A dermoscopic photograph of a skin lesion: 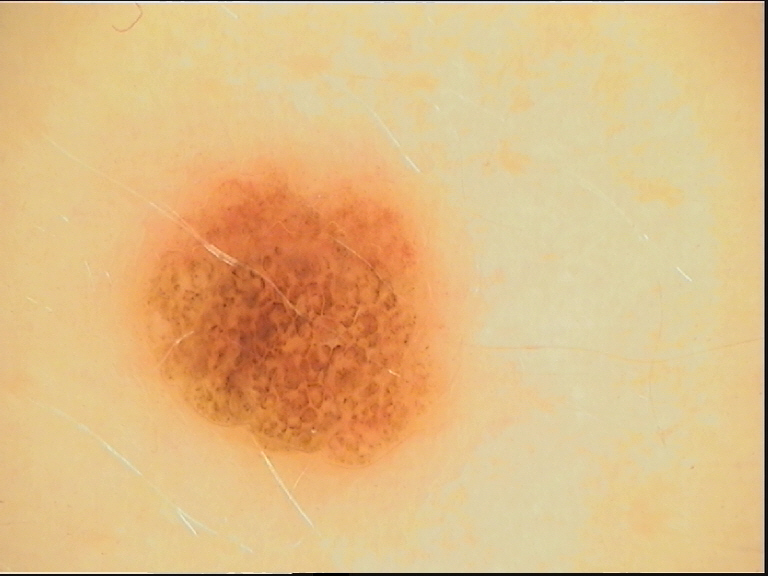Consistent with a benign lesion — a dysplastic compound nevus.